The patient is Fitzpatrick skin type II · a female patient aged 73-77 · contact-polarized dermoscopy of a skin lesion.
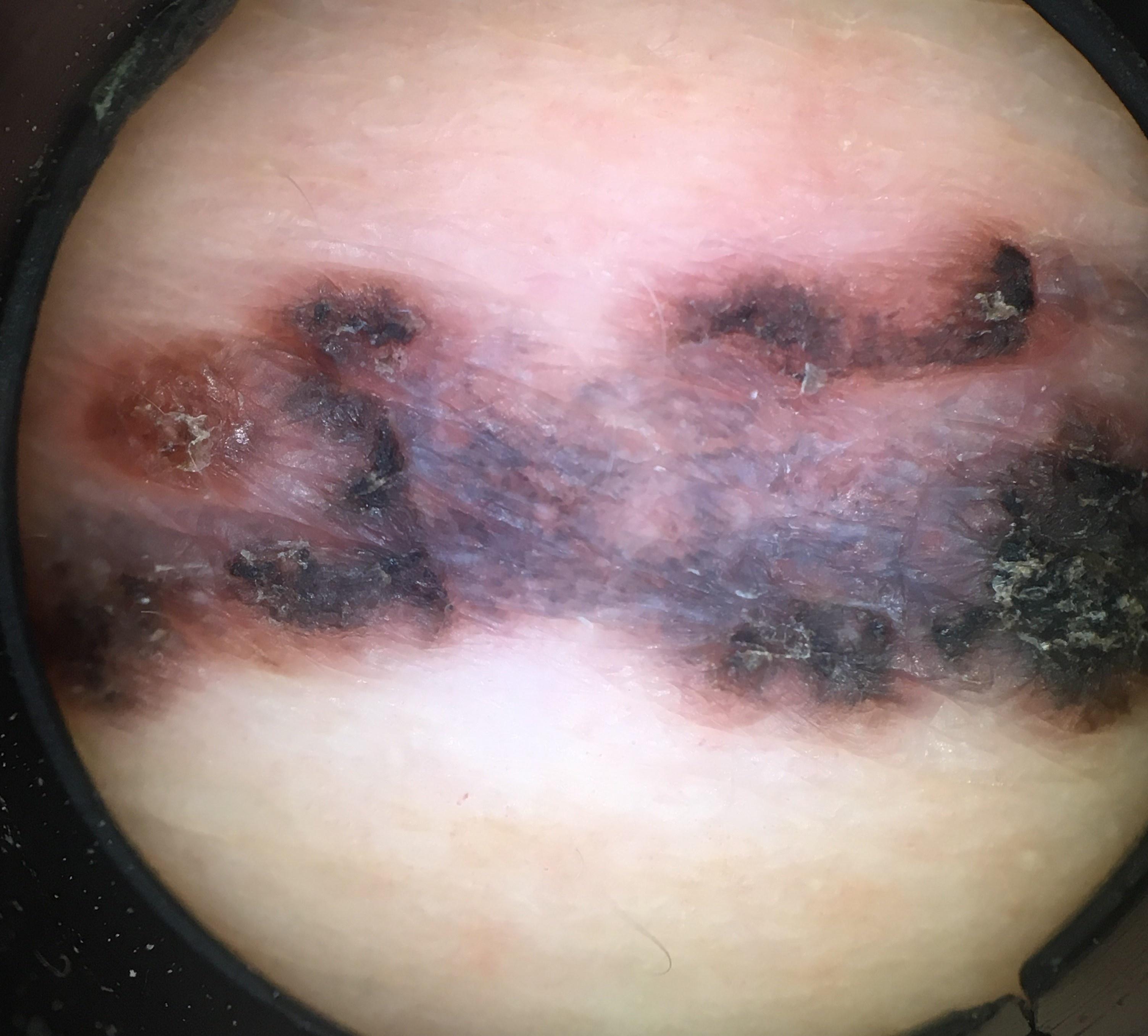The lesion is on the trunk. Histopathologically confirmed as a melanoma.